A dermoscopic photograph of a skin lesion.
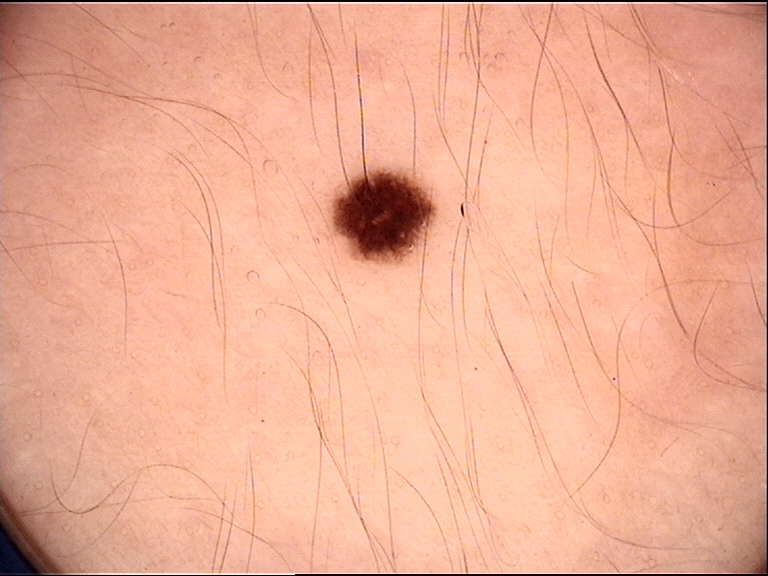Conclusion:
The diagnosis was a banal lesion — a junctional nevus.